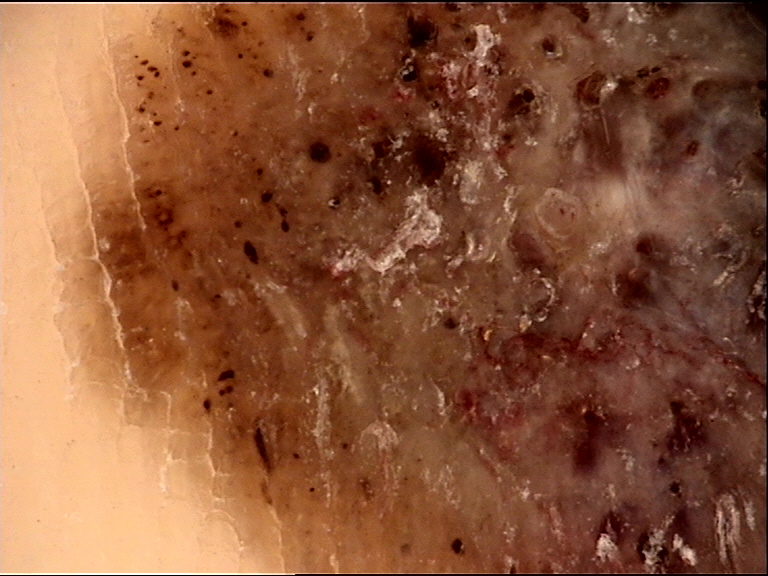| feature | finding |
|---|---|
| diagnosis | acral nodular melanoma (biopsy-proven) |